Close-up view. The lesion involves the back of the hand. The patient also reports shortness of breath, joint pain, mouth sores and fatigue. Reported lesion symptoms include itching. Reported duration is more than five years. The contributor is 50–59, female. The patient considered this a rash.
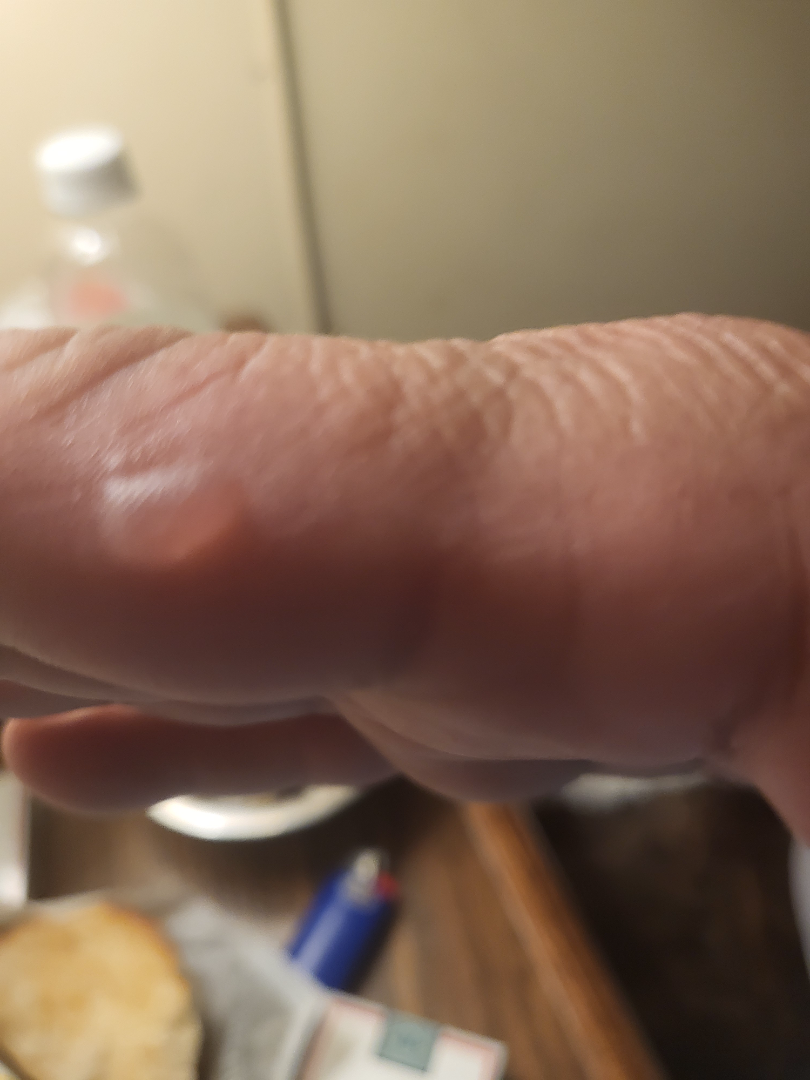differential:
  leading:
    - vesicles